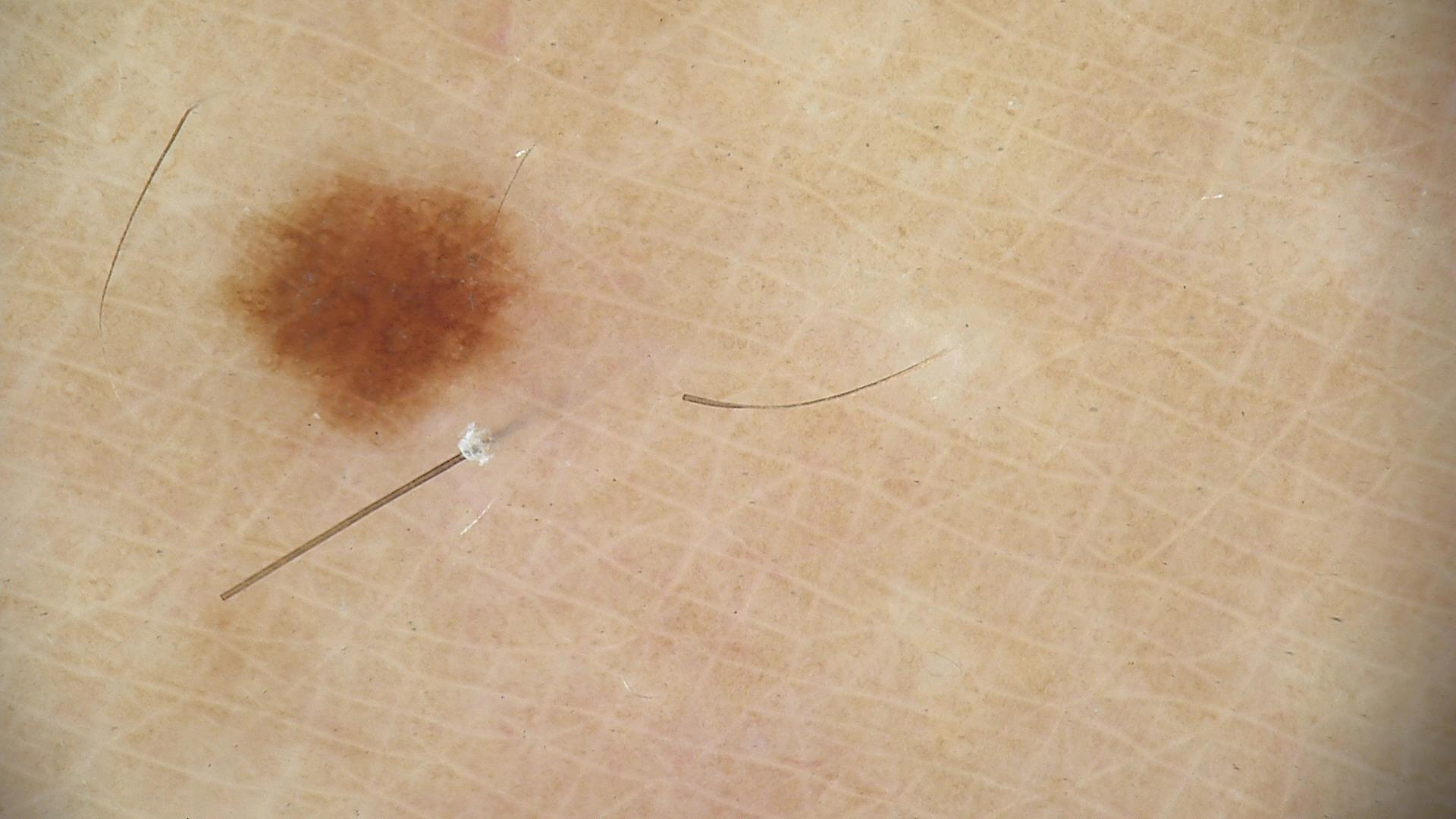Impression:
The diagnostic label was a dysplastic junctional nevus.